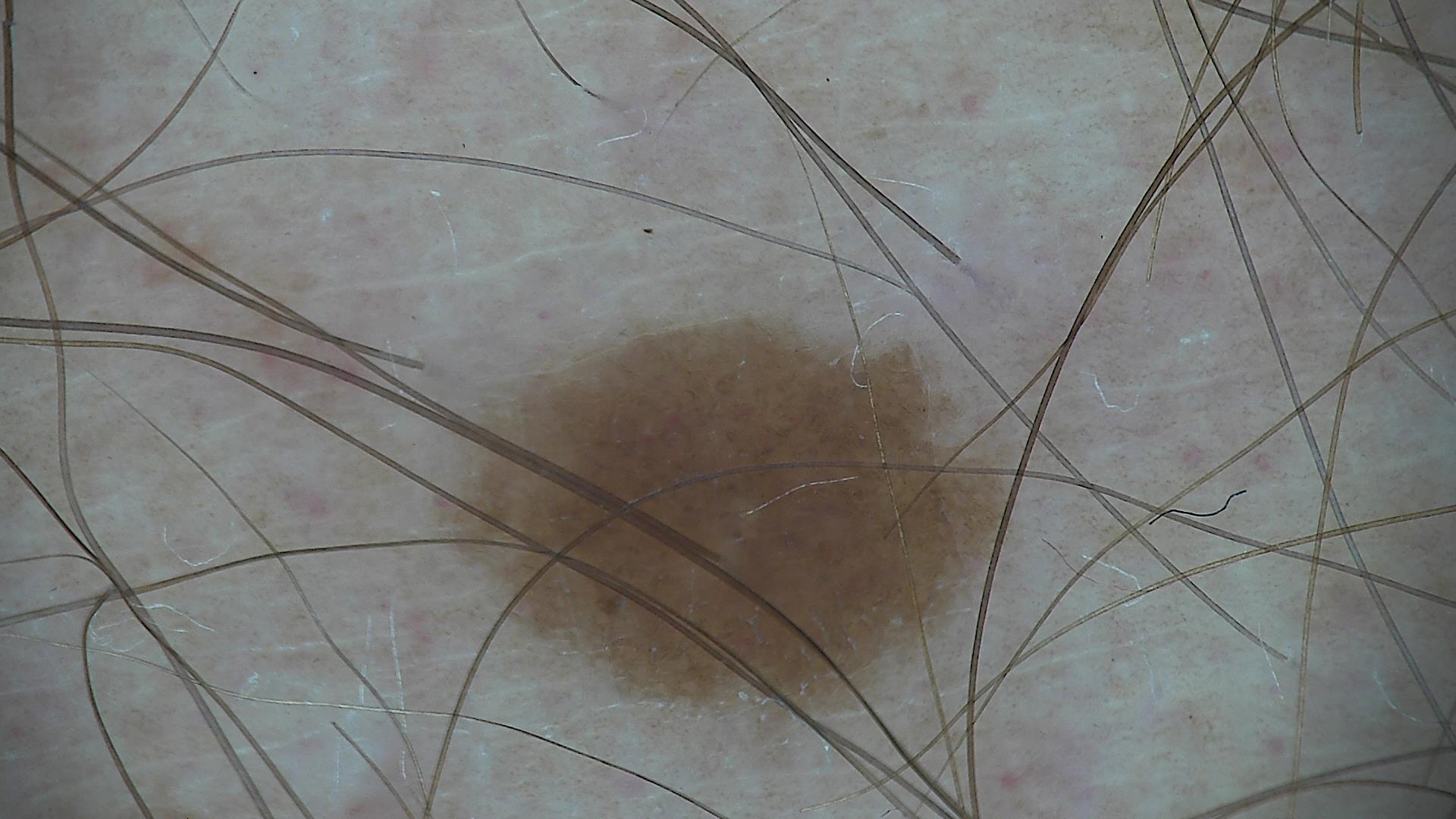A dermatoscopic image of a skin lesion. The diagnostic label was a dysplastic junctional nevus.